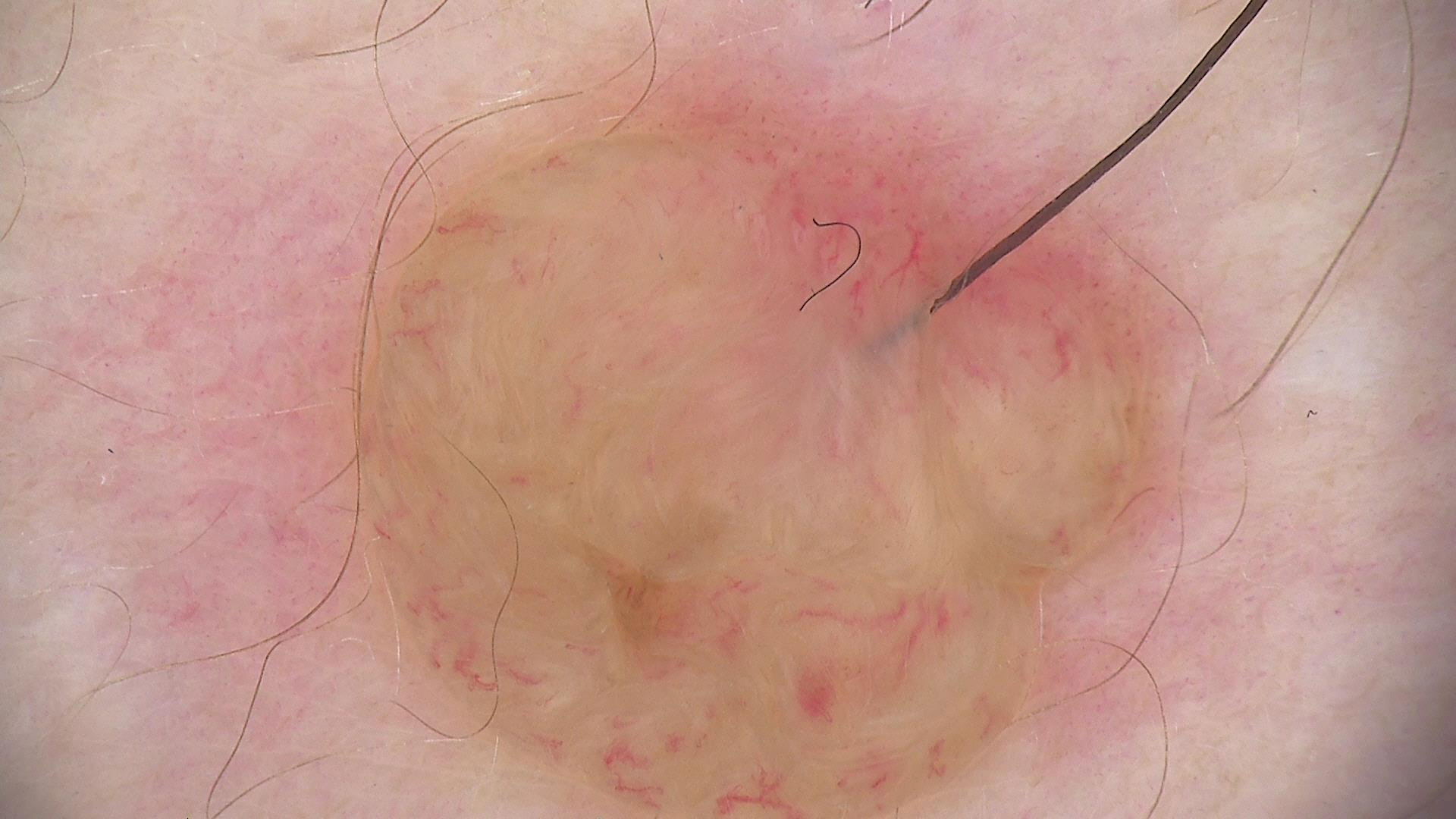The diagnosis was a banal lesion — a dermal nevus.